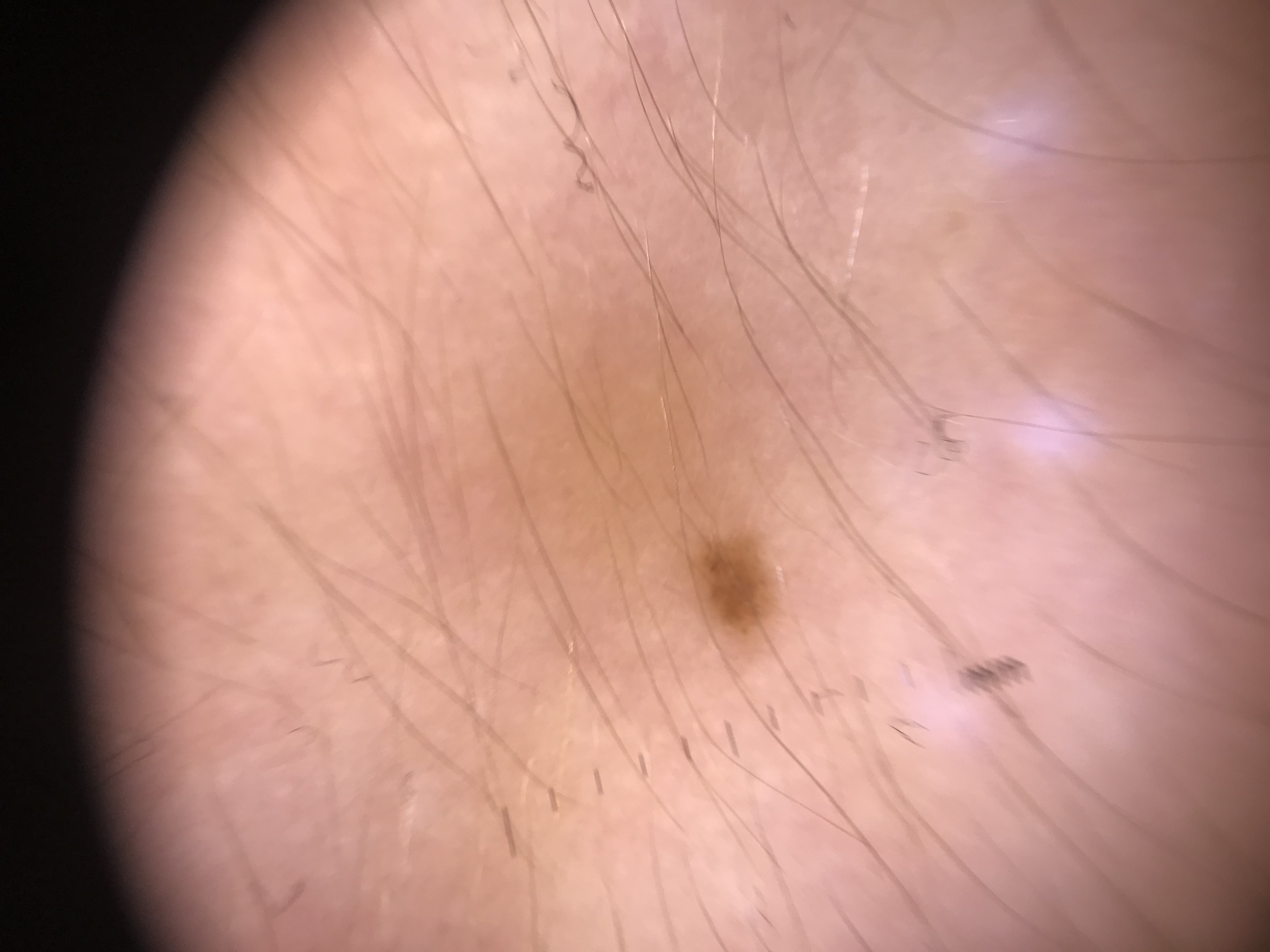The diagnosis was a banal lesion — a junctional nevus.